Located on the leg; the contributor notes the lesion is rough or flaky; reported lesion symptoms include itching; female patient, age 30–39; the patient described the issue as a rash; the patient also reports shortness of breath, fatigue and joint pain; reported duration is more than one year; the photograph is a close-up of the affected area:
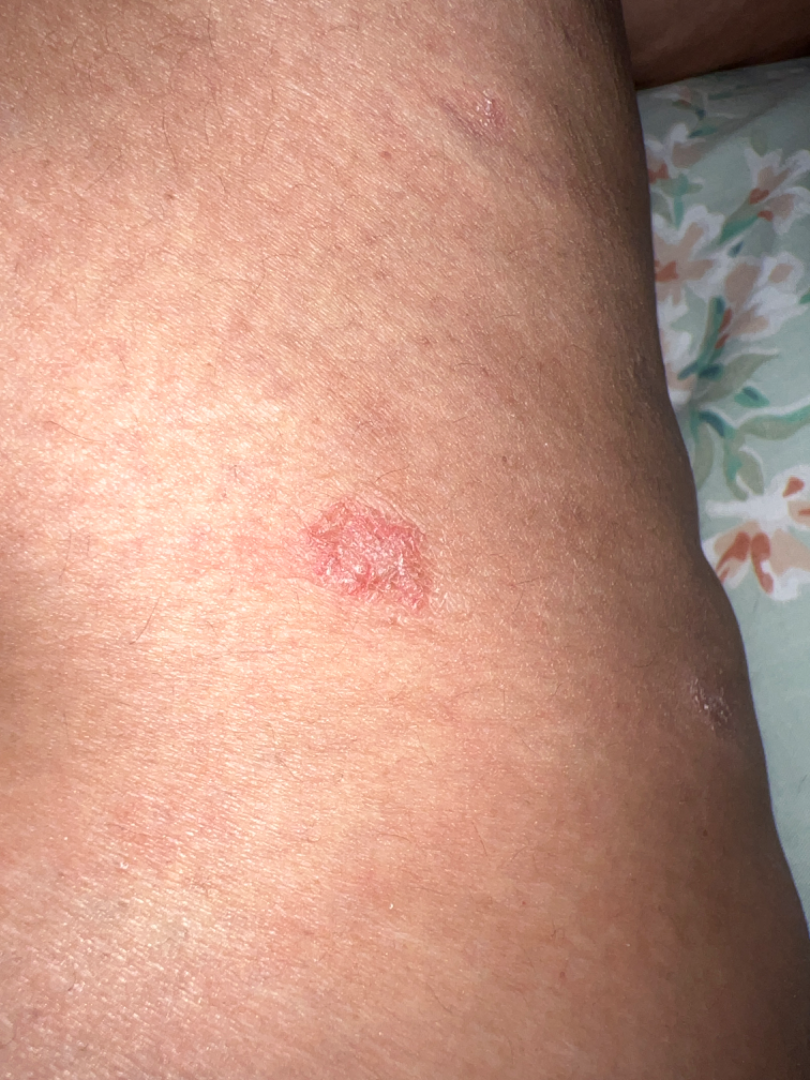On remote review of the image, favoring Porokeratosis; also raised was Actinic Keratosis; a remote consideration is SCC/SCCIS.